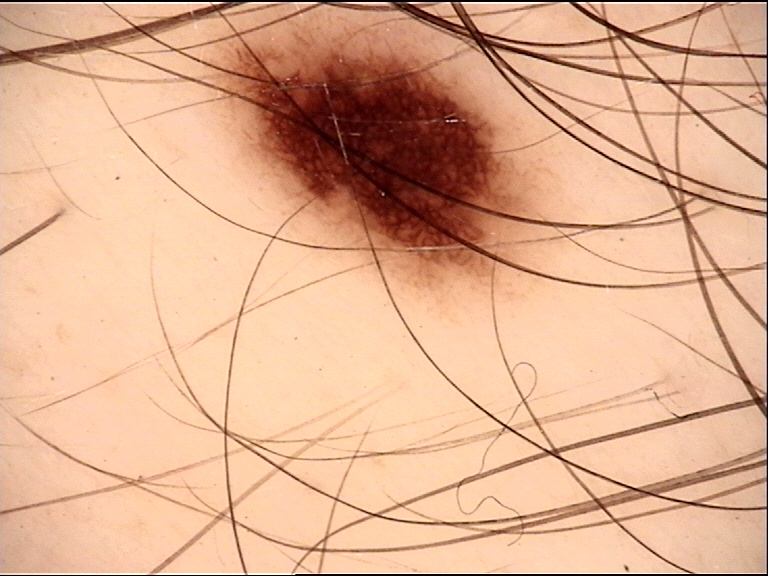Q: What is this lesion?
A: junctional nevus (expert consensus)